Located on the palm · the photo was captured at a distance · female contributor, age 50–59:
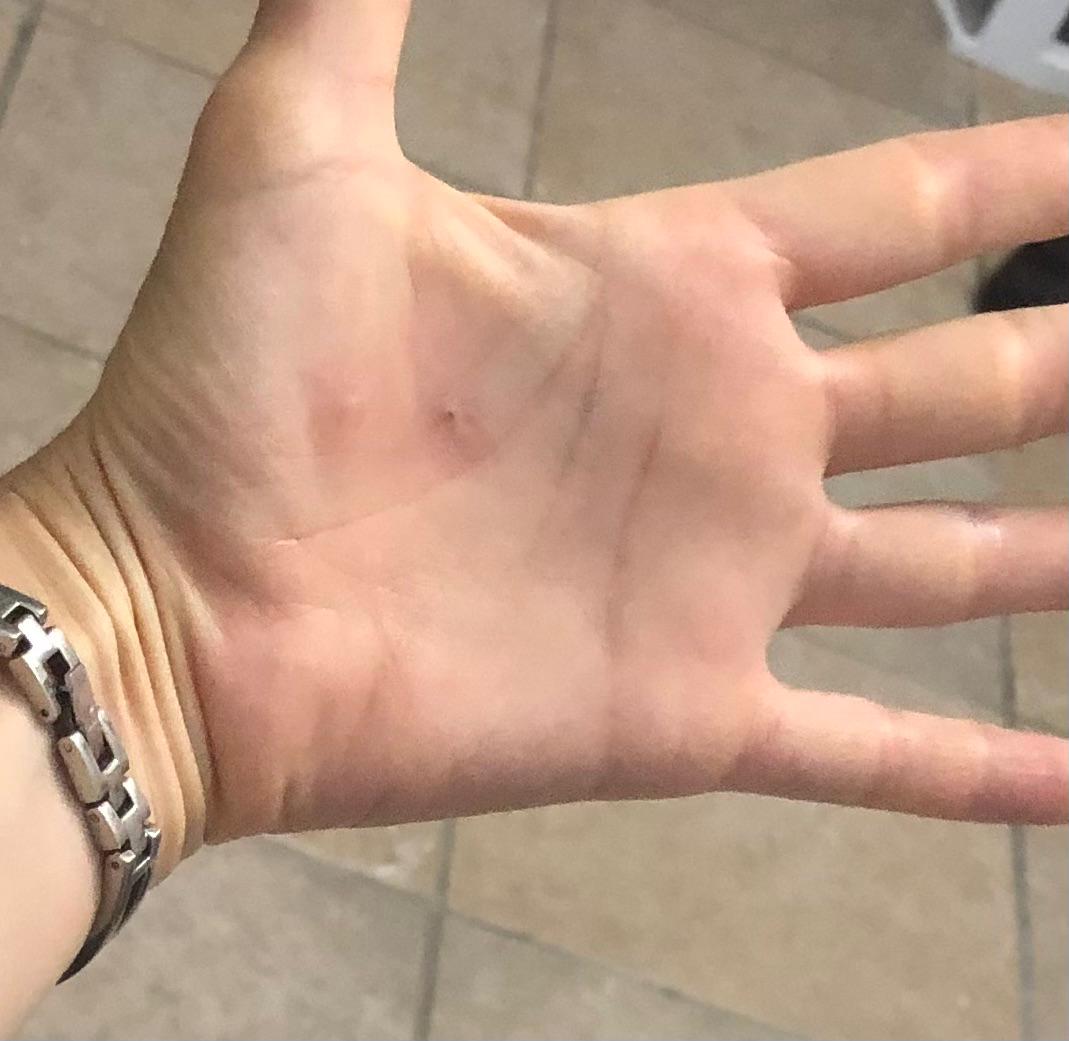Q: What is the dermatologist's impression?
A: Eczema (favored); Irritant Contact Dermatitis (considered)